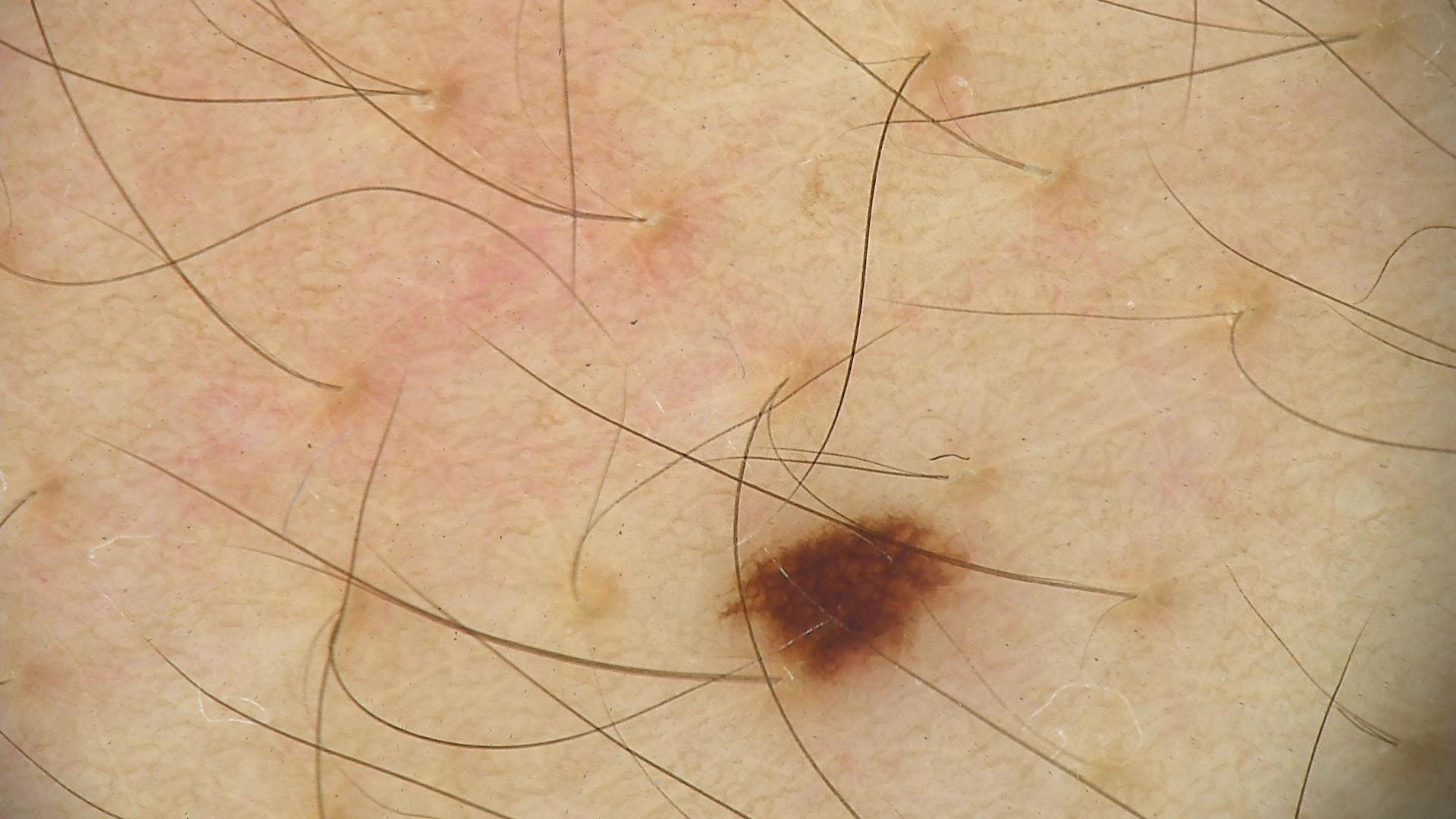image type = dermoscopy | classification = banal | assessment = junctional nevus (expert consensus).